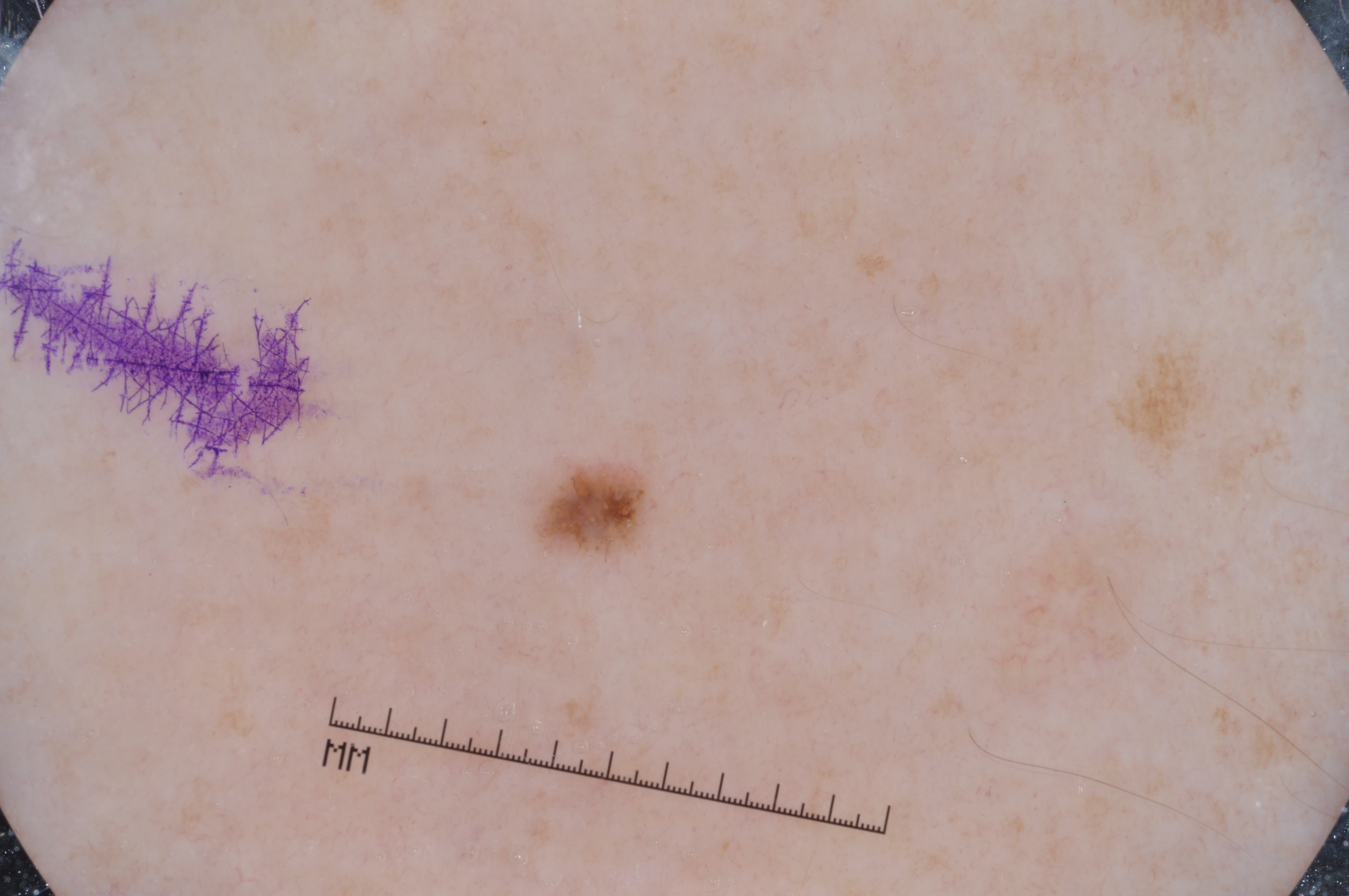| field | value |
|---|---|
| modality | dermoscopy |
| lesion location | bbox(548, 469, 643, 539) |
| diagnosis | a melanocytic nevus |